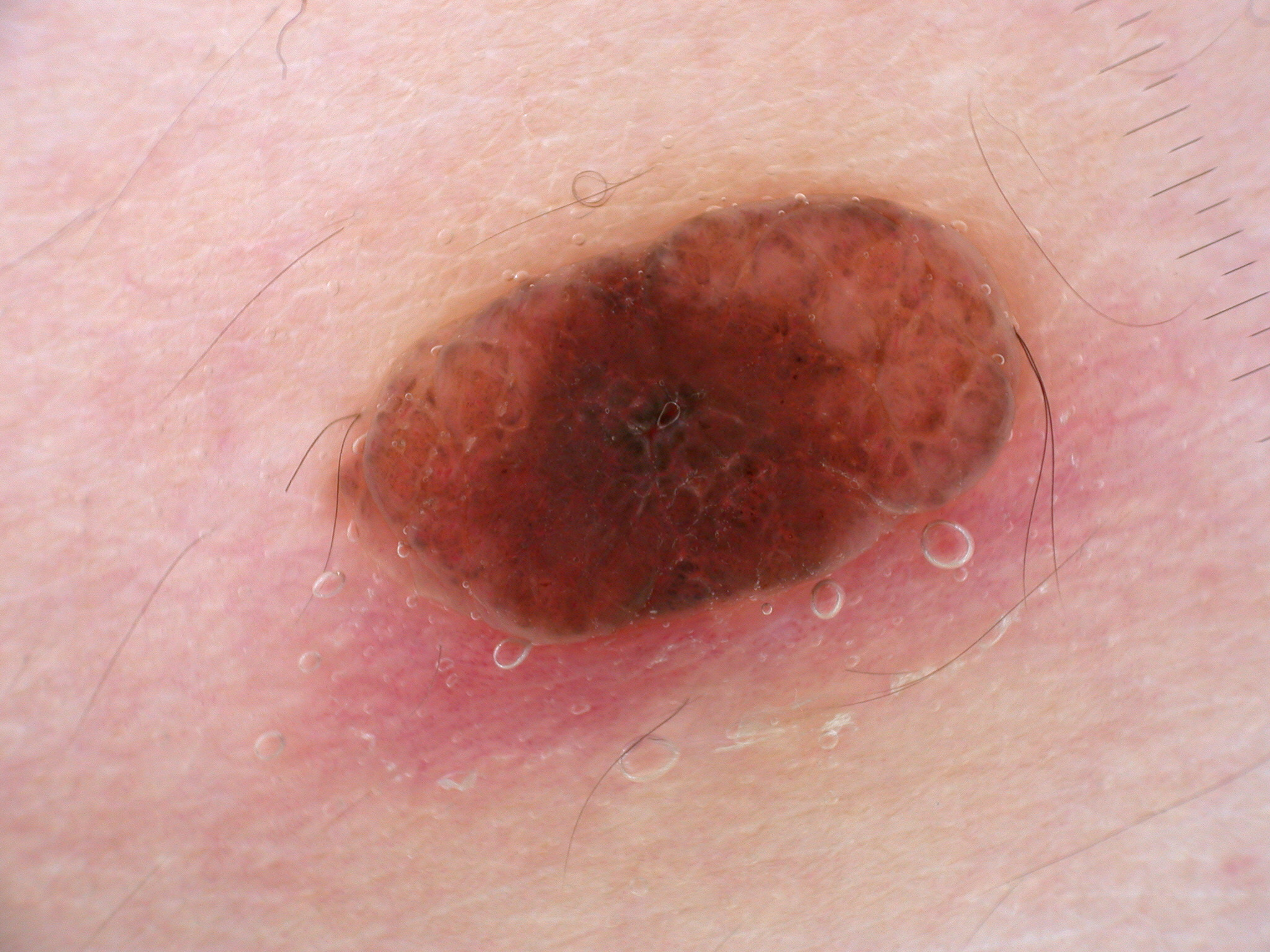Image and clinical context:
Dermoscopy of a skin lesion. Dermoscopic review identifies no milia-like cysts, streaks, globules, pigment network, or negative network. Lesion location: [326, 188, 1022, 646].
Conclusion:
Clinically diagnosed as a melanocytic nevus, a benign skin lesion.